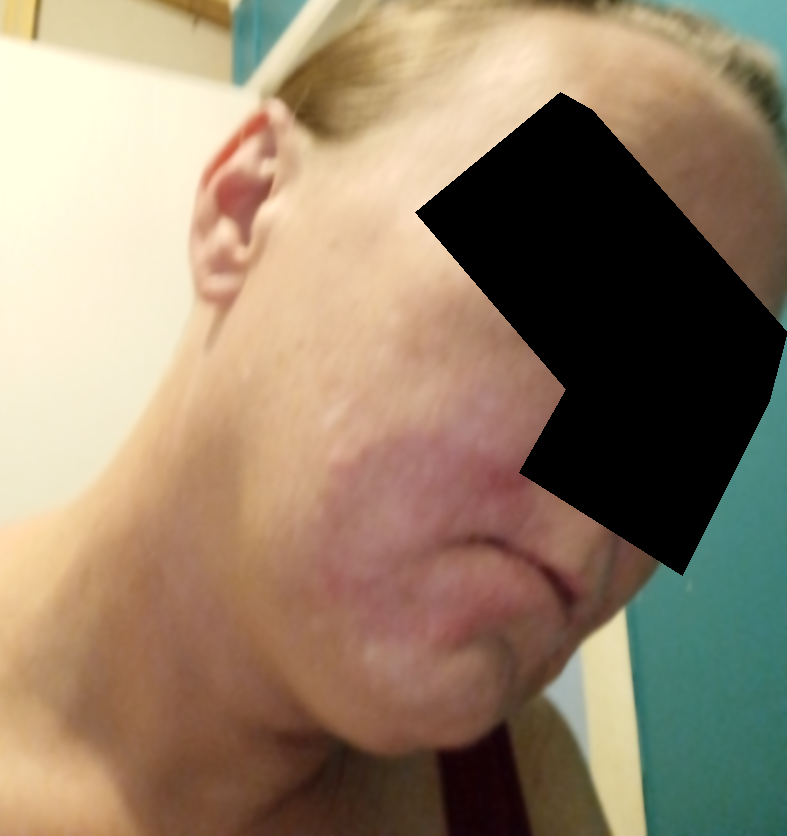Q: Could the case be diagnosed?
A: could not be assessed